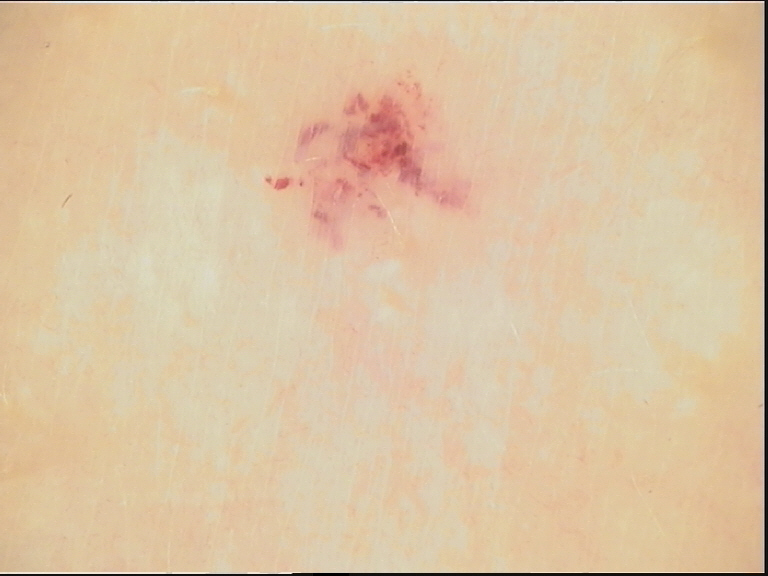label = hemangioma (expert consensus).